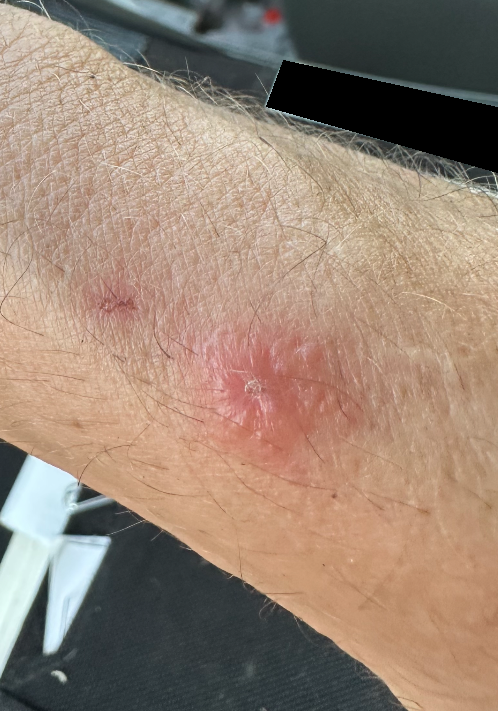| key | value |
|---|---|
| image framing | close-up |
| patient | male, age 50–59 |
| described texture | raised or bumpy and fluid-filled |
| patient describes the issue as | a rash |
| skin tone | FST III; lay graders estimated Monk skin tone scale 1–2 |
| anatomic site | arm |
| associated systemic symptoms | none reported |
| duration | less than one week |
| differential diagnosis | Insect Bite (possible); Allergic Contact Dermatitis (possible); Molluscum Contagiosum (lower probability) |